An image taken at a distance; the lesion involves the leg: 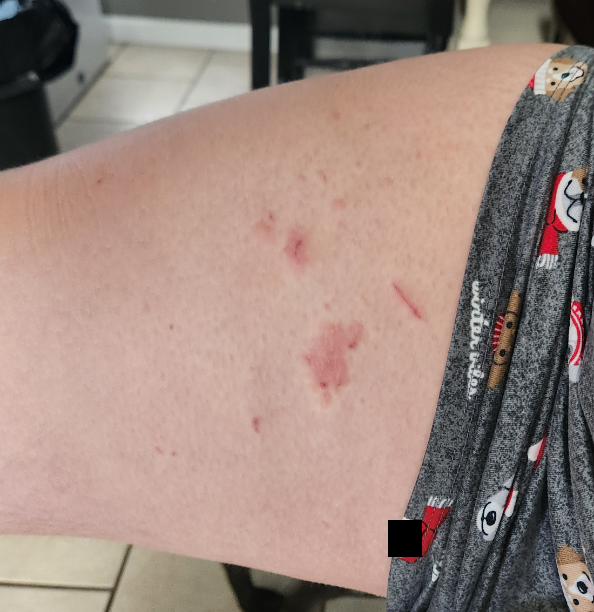* lesion symptoms — itching and enlargement
* skin tone — Fitzpatrick II
* dermatologist impression — Allergic Contact Dermatitis (0.54); Eczema (0.23); Psoriasis (0.23)